Located on the back of the torso, front of the torso, head or neck and arm. An image taken at an angle. The patient reports bothersome appearance, itching and enlargement. Texture is reported as raised or bumpy. Female subject, age 18–29. Reported duration is less than one week:
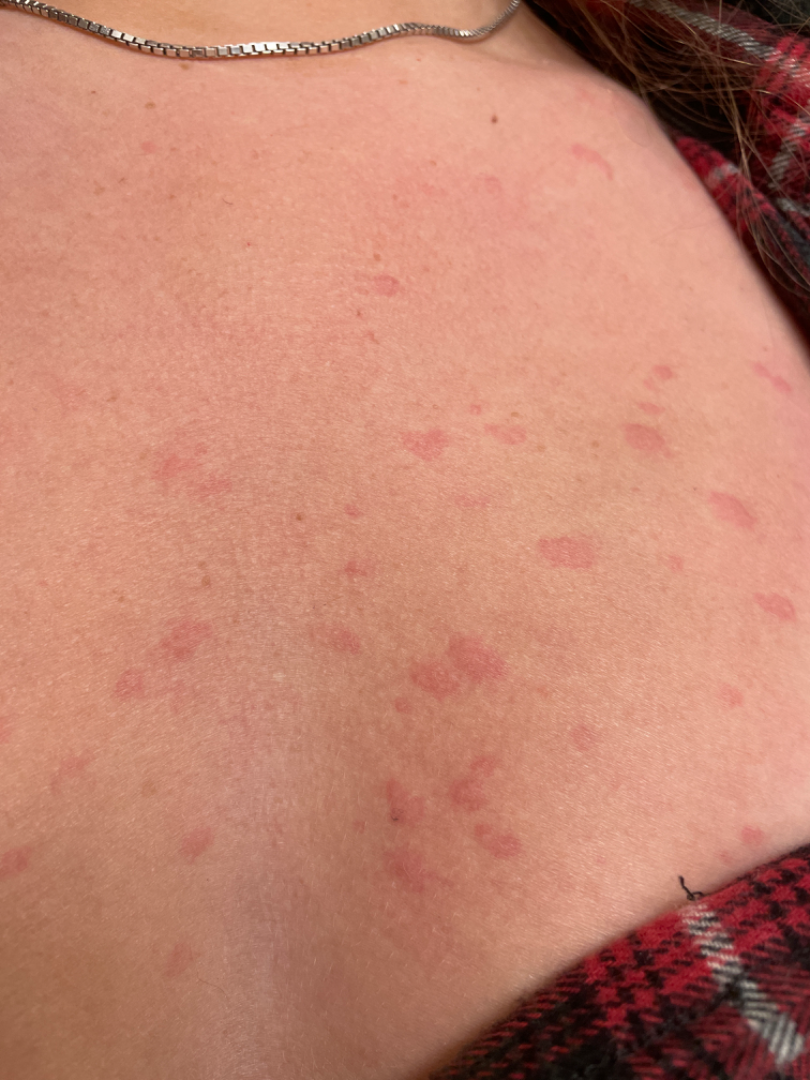Findings:
The skin condition could not be confidently assessed from this image.